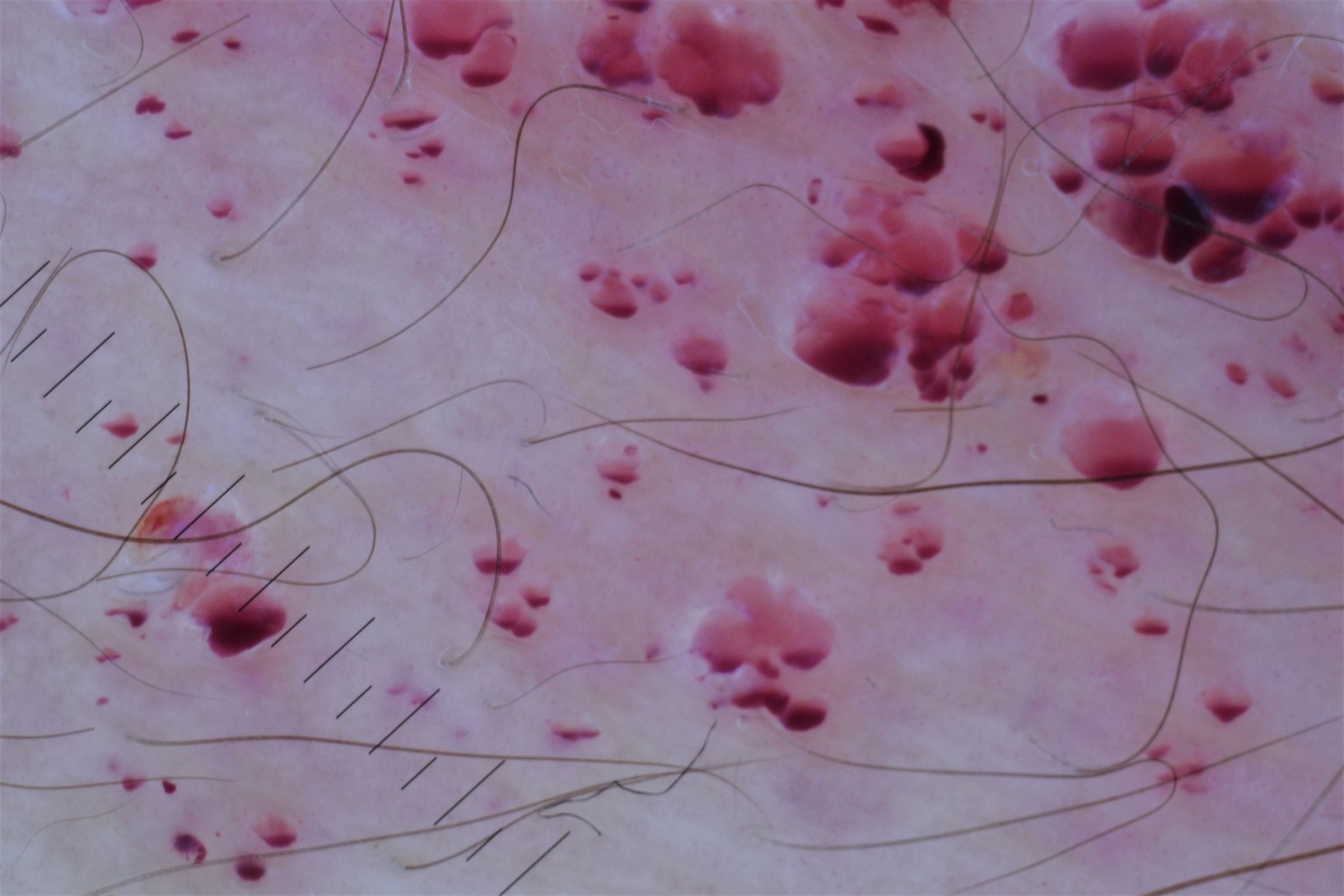Classified as a lymphangioma.